A subject in their 40s; a clinical photo of a skin lesion taken with a smartphone.
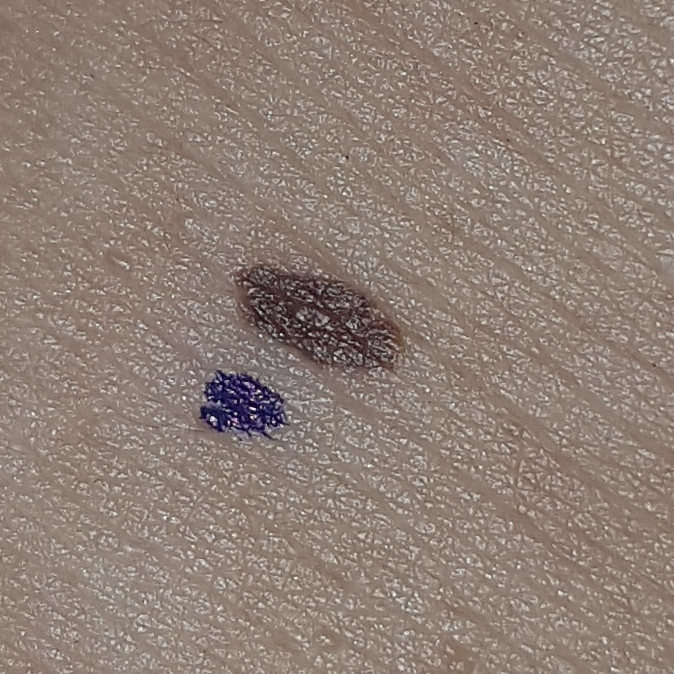Patient and lesion: The lesion is on the abdomen. Per patient report, the lesion has grown. Conclusion: The clinical impression was a benign skin lesion — a nevus.